Female patient, age 30–39. This image was taken at an angle:
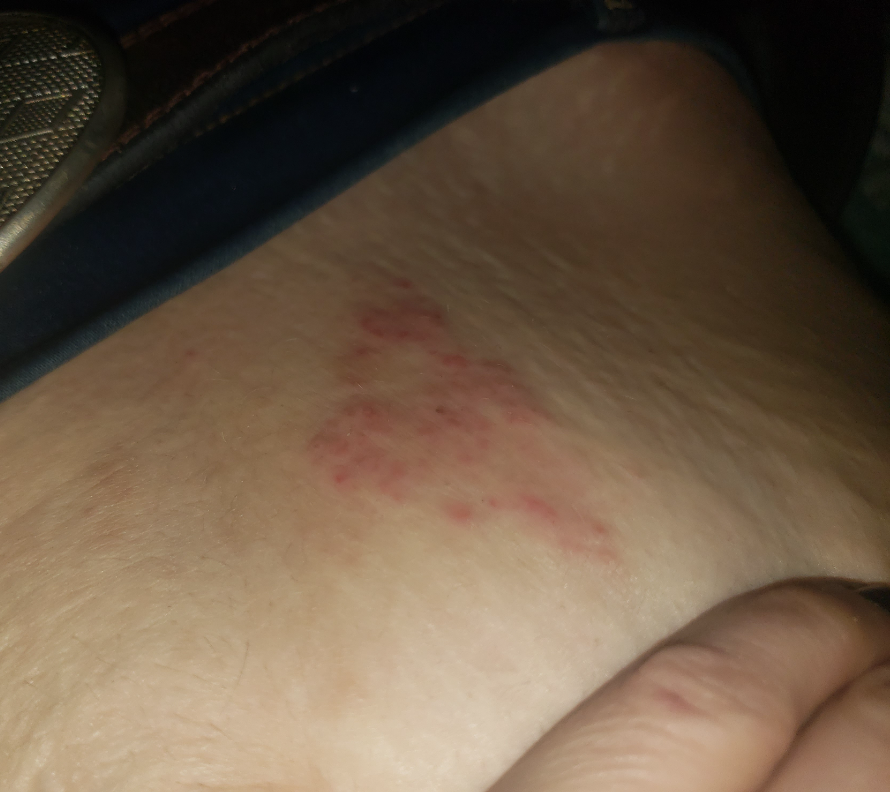Assessment:
Most likely Herpes Zoster; also consider Tinea; with consideration of Impetigo.